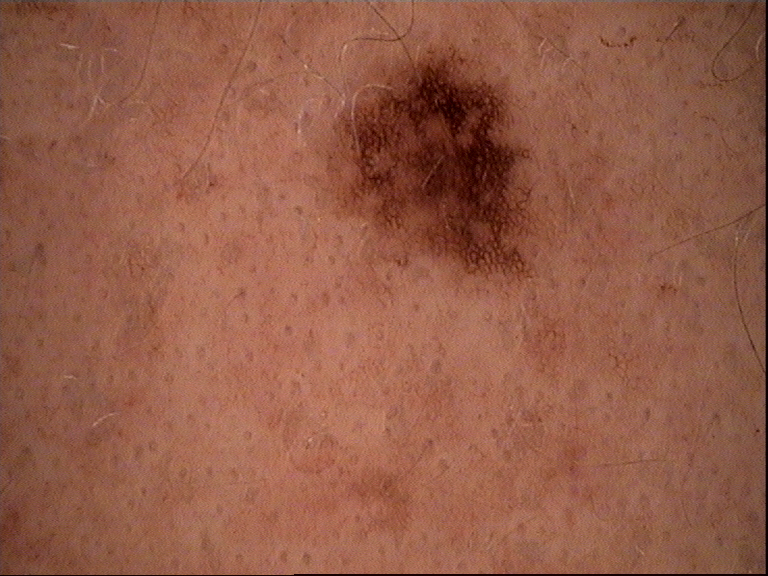{"image": "dermoscopy", "diagnosis": {"name": "dysplastic junctional nevus", "code": "jd", "malignancy": "benign", "super_class": "melanocytic", "confirmation": "expert consensus"}}